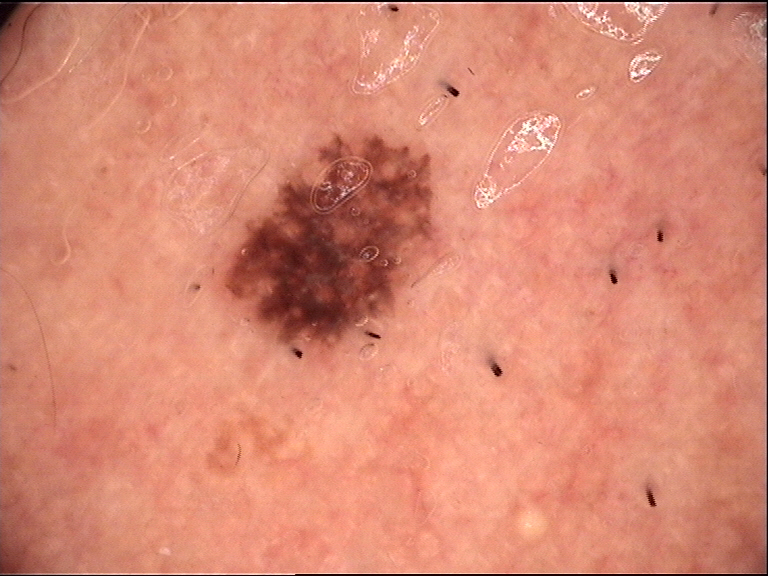The diagnosis was a dysplastic compound nevus.